A male subject aged 37 — 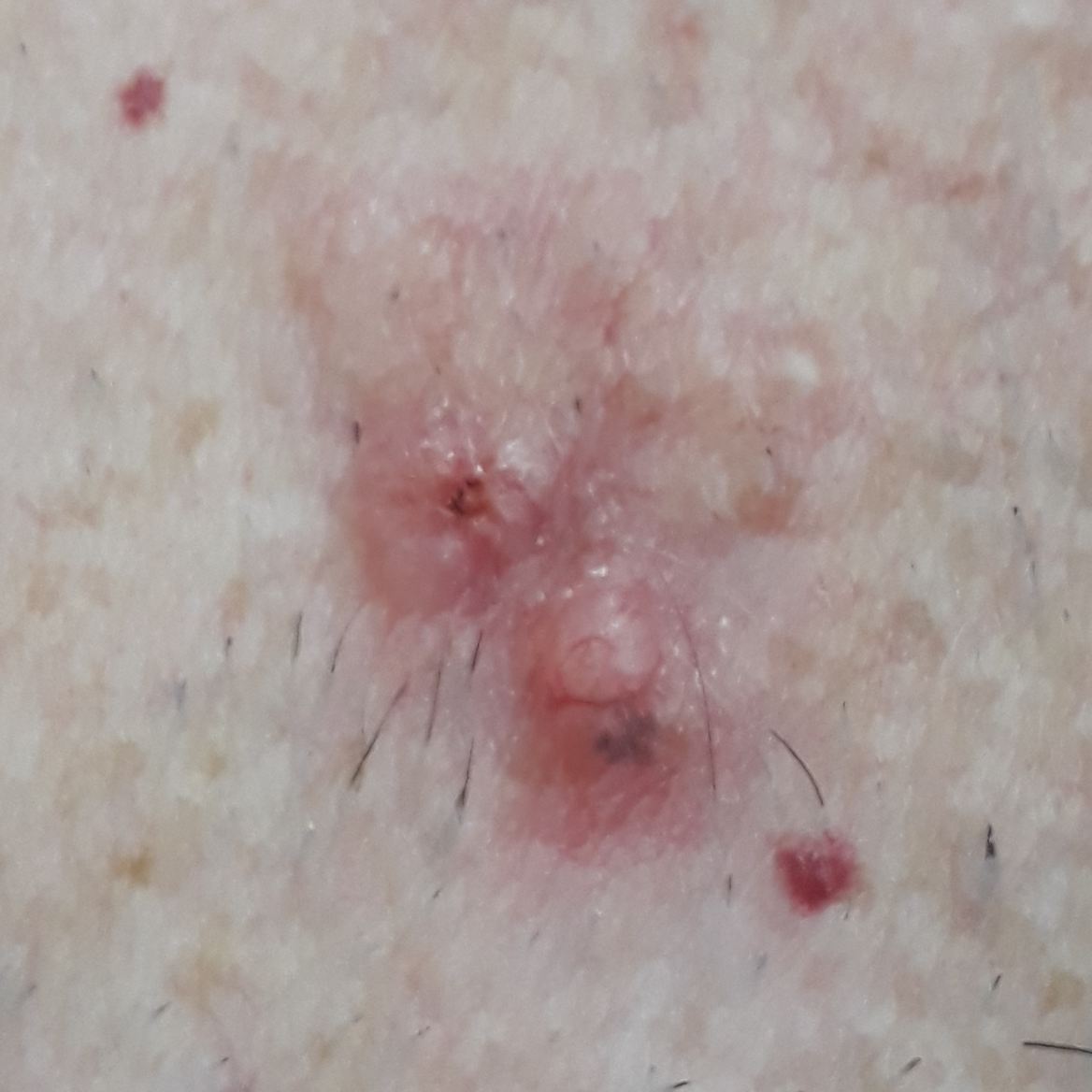Summary:
Per patient report, the lesion is elevated and itches, but does not hurt and has not bled.
Diagnosis:
Biopsy-confirmed as a basal cell carcinoma.